Female subject, age 18–29. This image was taken at an angle. The lesion involves the leg, front of the torso and arm — 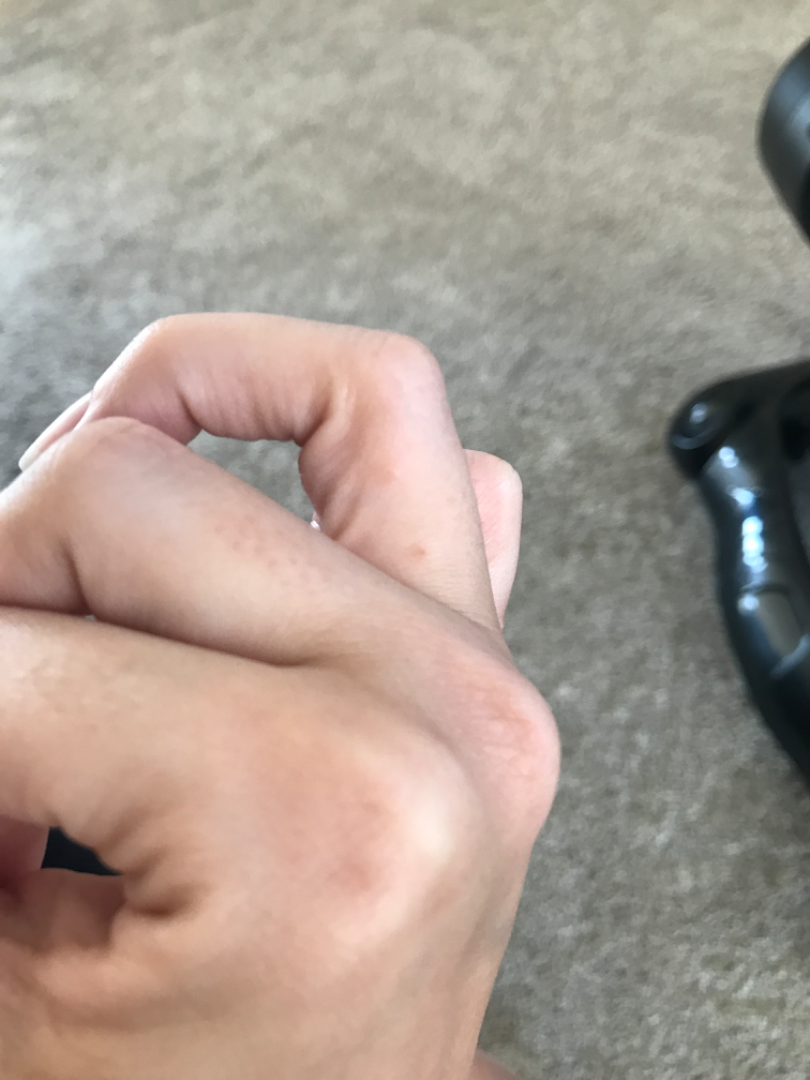Patient information:
Symptoms reported: itching. Present for one to four weeks. Texture is reported as fluid-filled.
Review:
On remote review of the image, most likely Eczema; the differential also includes Scabies.